Recorded as Fitzpatrick II — 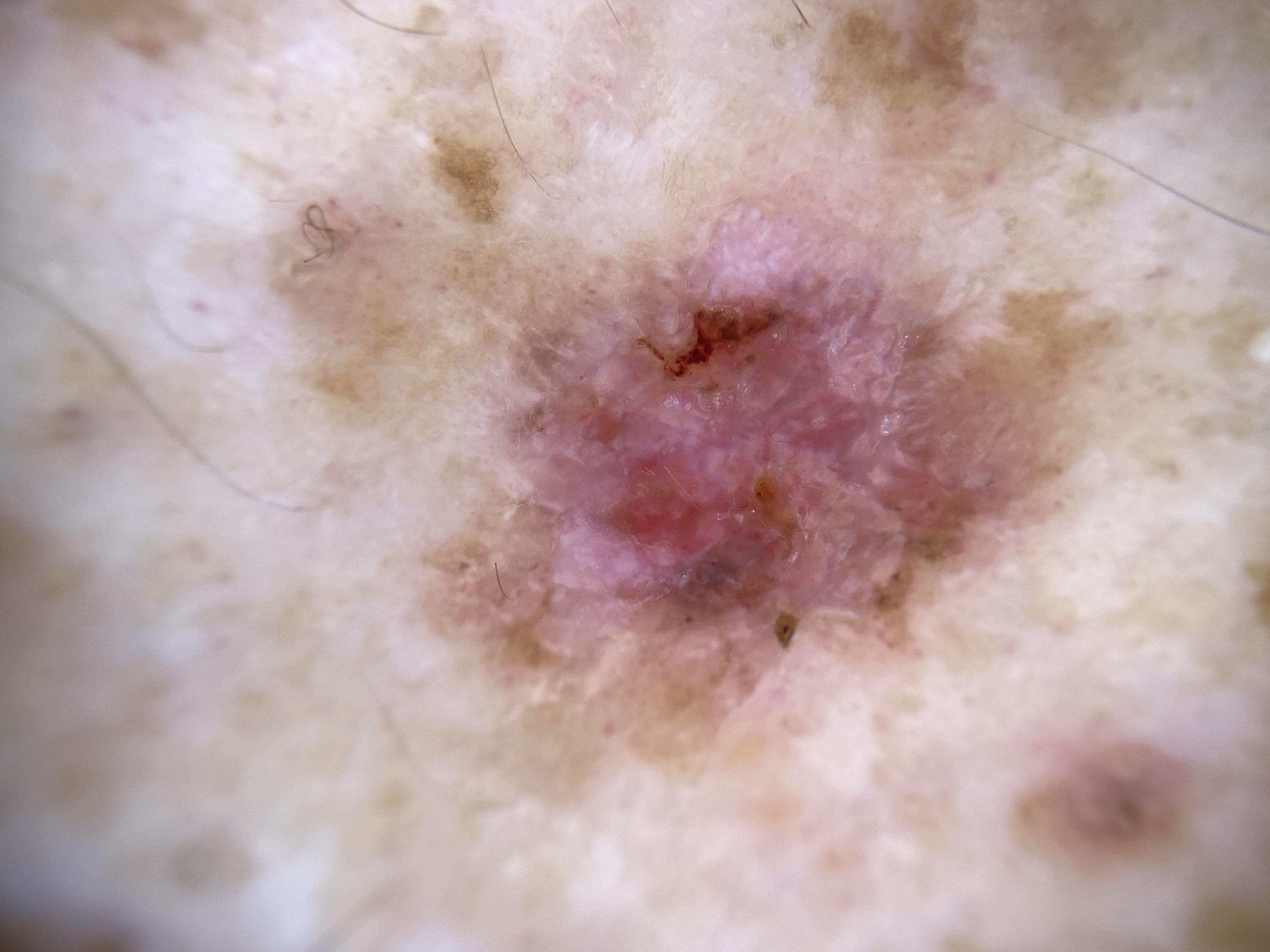The lesion is on a lower extremity.
Histopathologically confirmed as a basal cell carcinoma.